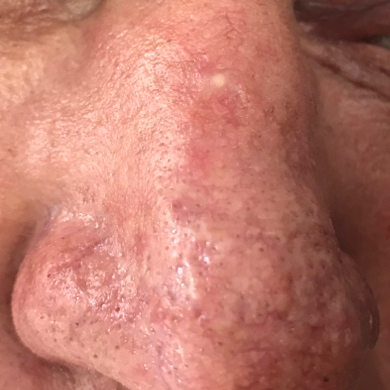patient: female, aged 61
image type: smartphone clinical photo
body site: the nose
size: 4x4 mm
symptoms: itching, bleeding, elevation / no pain
diagnostic label: basal cell carcinoma (biopsy-proven)